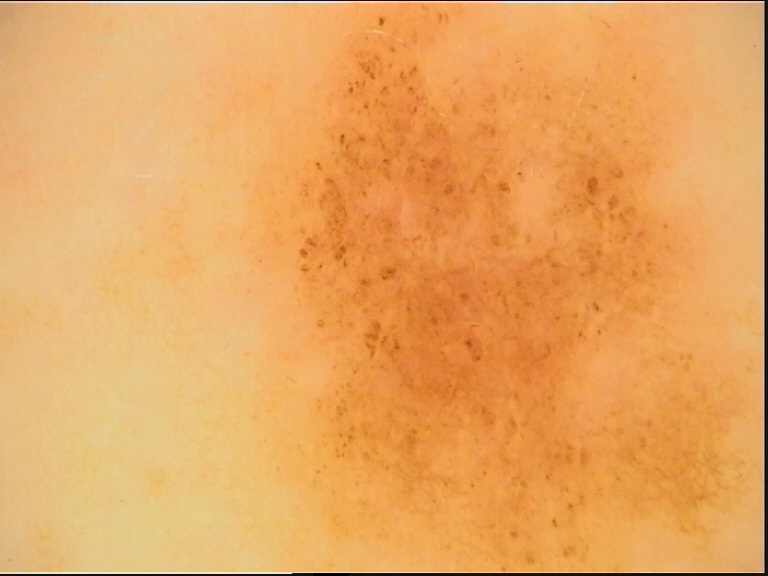Findings:
Dermoscopy of a skin lesion.
Conclusion:
The diagnostic label was a benign lesion — a dysplastic junctional nevus.